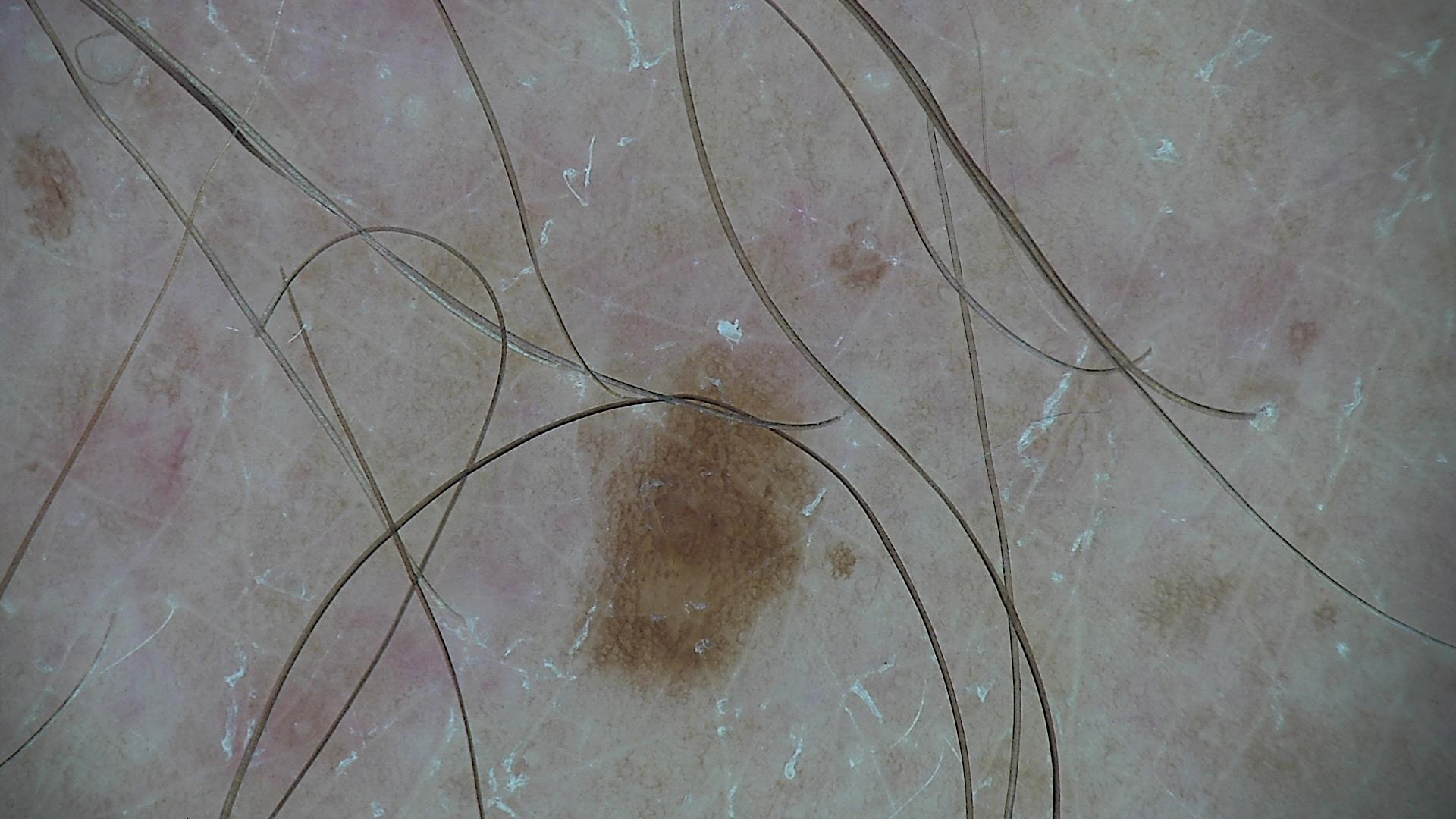Diagnosed as a dysplastic junctional nevus.